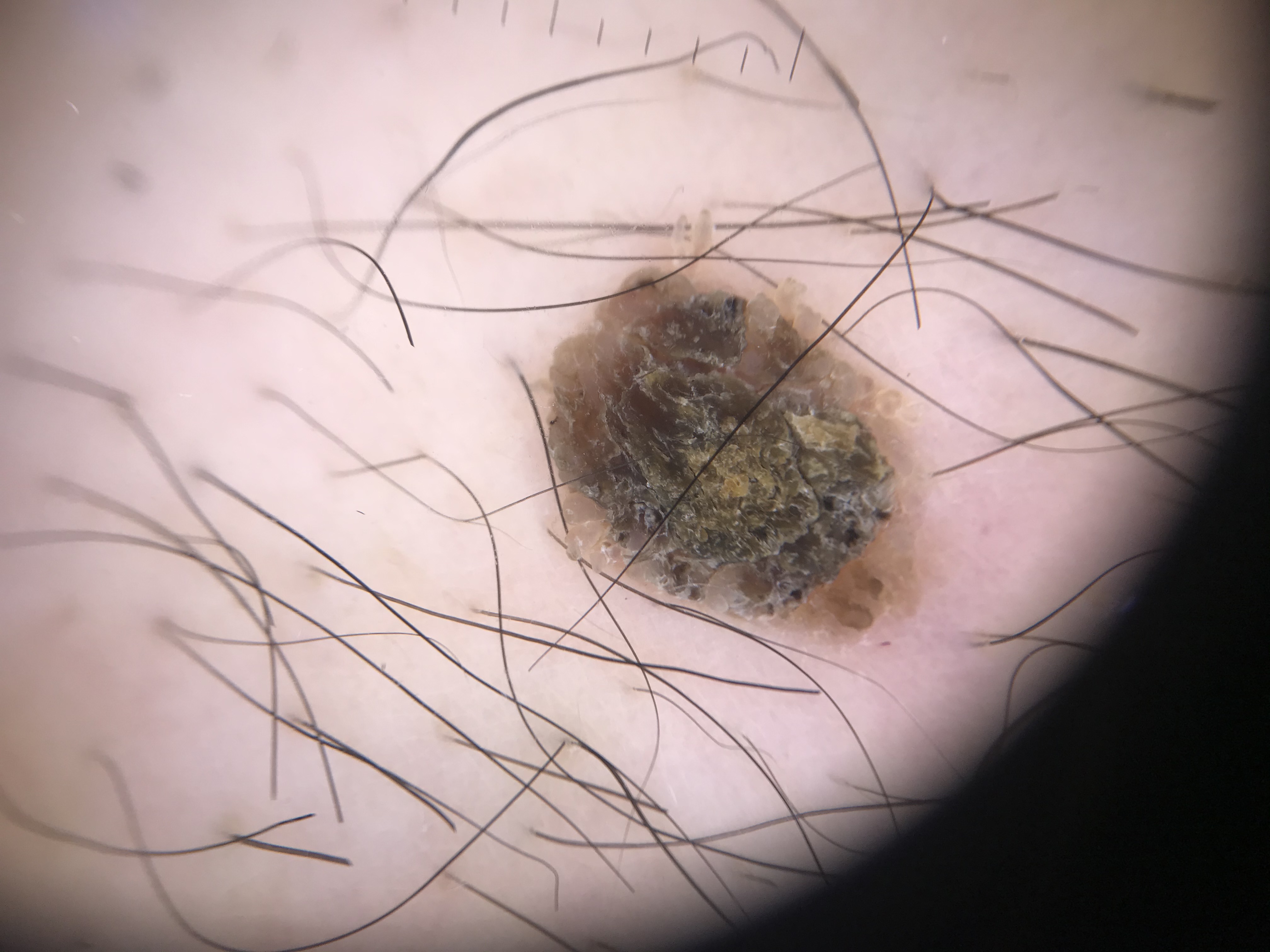The diagnostic label was a seborrheic keratosis.